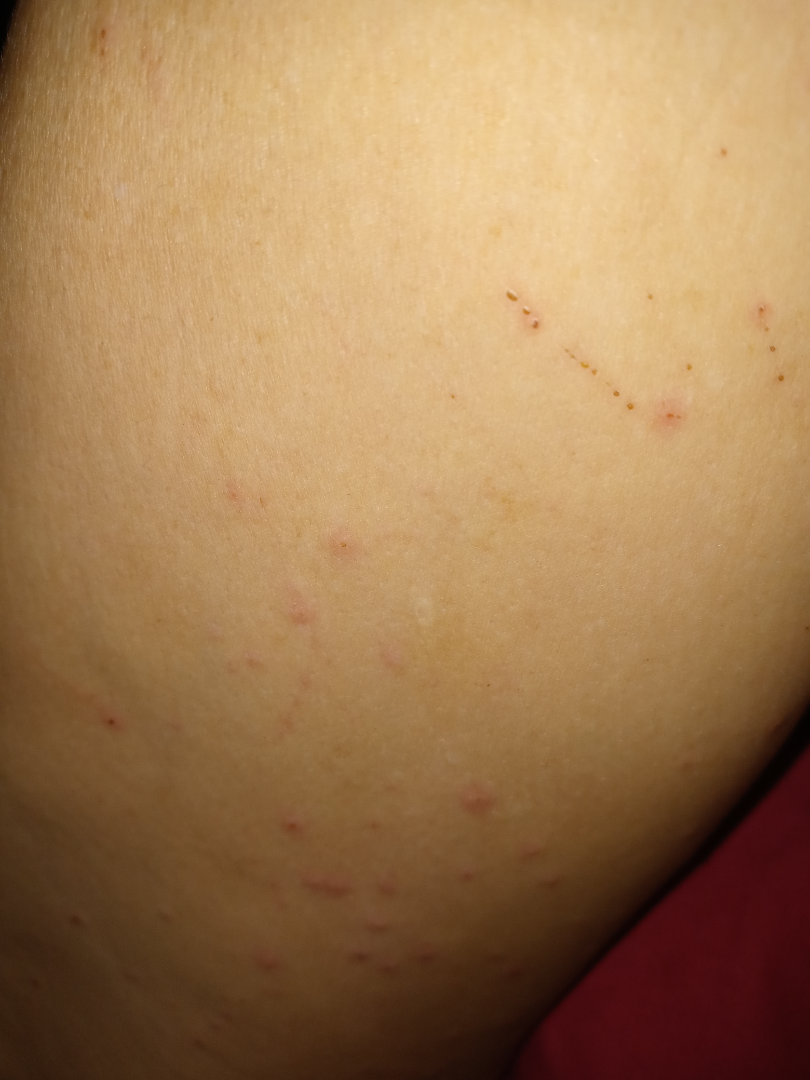shot_type: at an angle
differential:
  leading:
    - Hypersensitivity
  considered:
    - Insect Bite